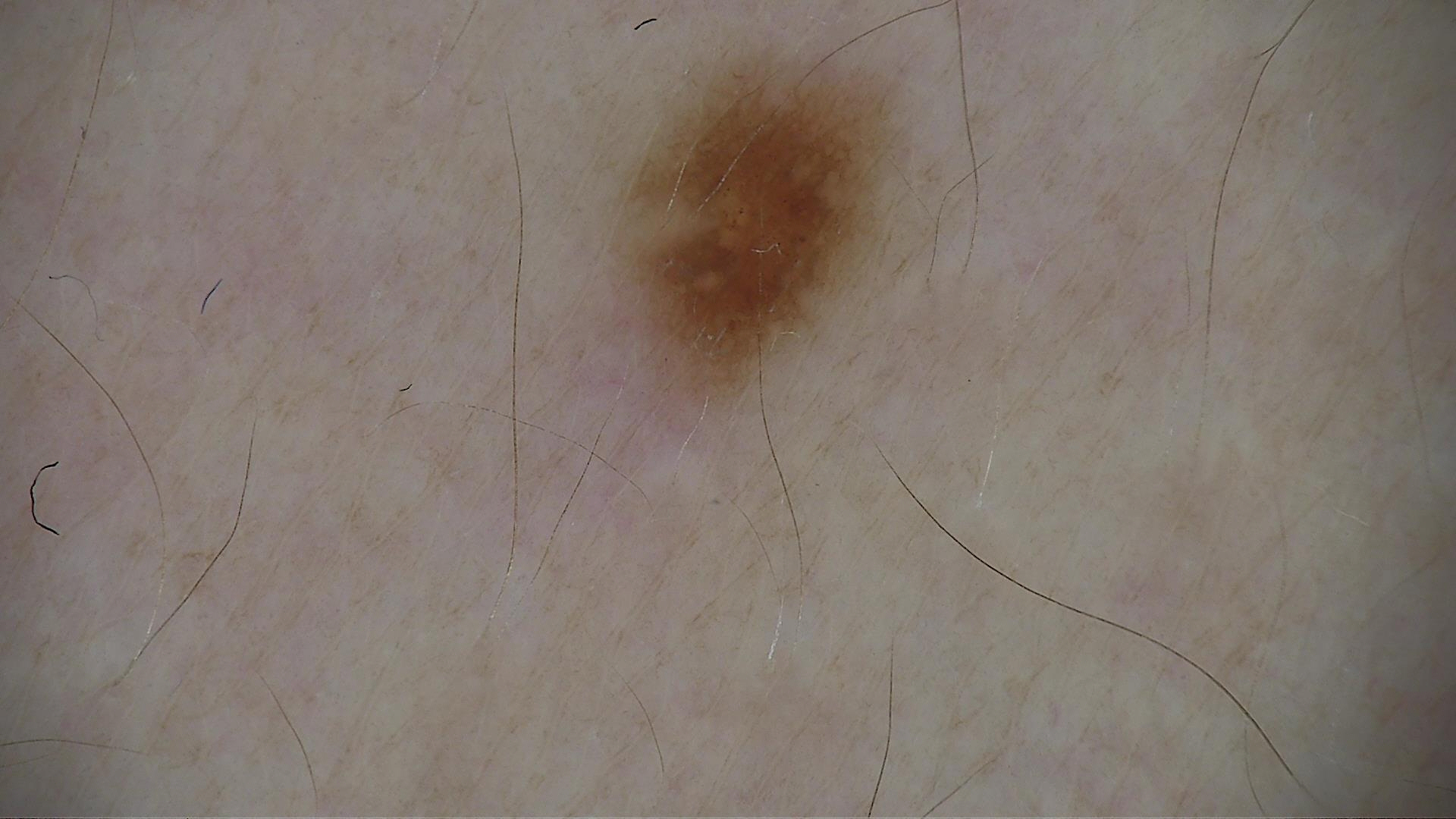{"image": "dermatoscopy", "diagnosis": {"name": "dysplastic junctional nevus", "code": "jd", "malignancy": "benign", "super_class": "melanocytic", "confirmation": "expert consensus"}}